A dermoscopic close-up of a skin lesion:
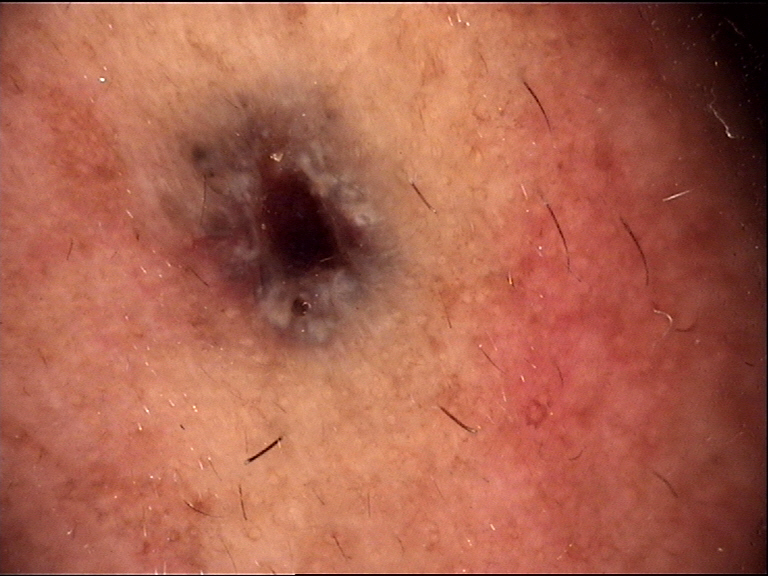Histopathology confirmed a keratinocytic, malignant lesion — a basal cell carcinoma.